A dermoscopic photograph of a skin lesion: 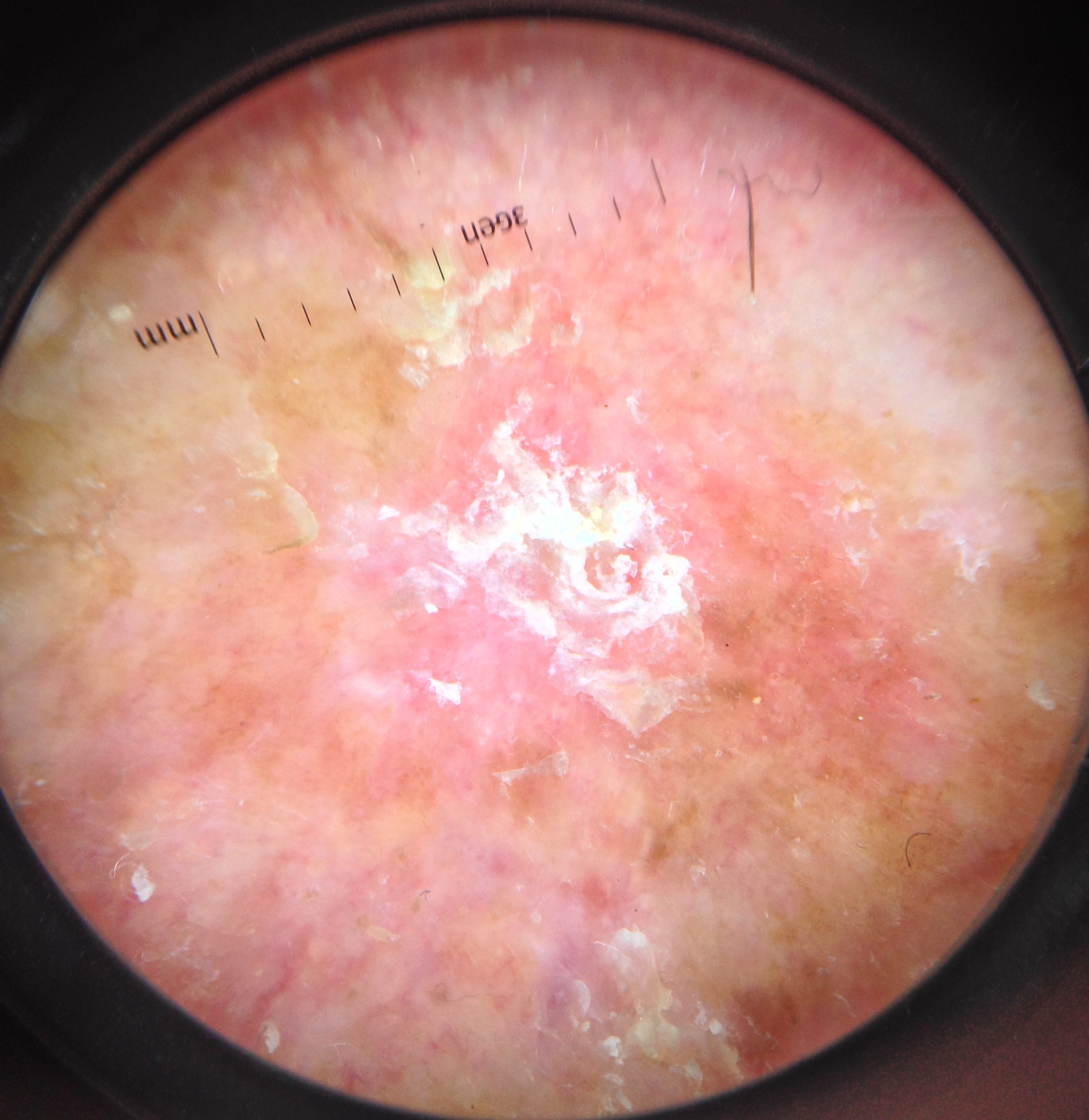Histopathologically confirmed as a keratinocytic lesion — a squamous cell carcinoma.